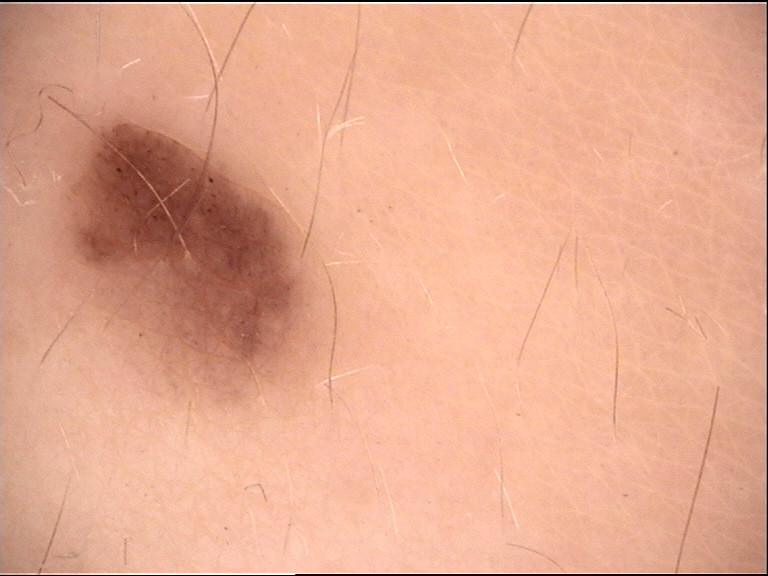Consistent with a junctional nevus.